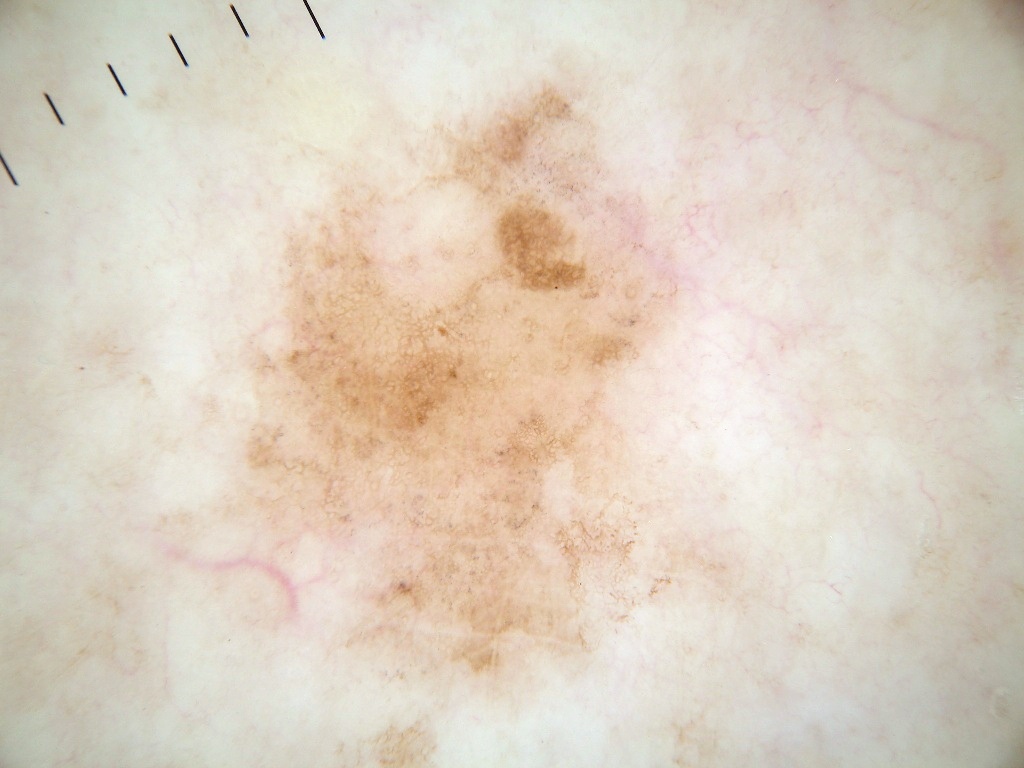image:
  modality: dermoscopy
lesion_location:
  bbox_xyxy:
    - 190
    - 50
    - 767
    - 766
diagnosis:
  malignancy: benign
  provenance: clinical